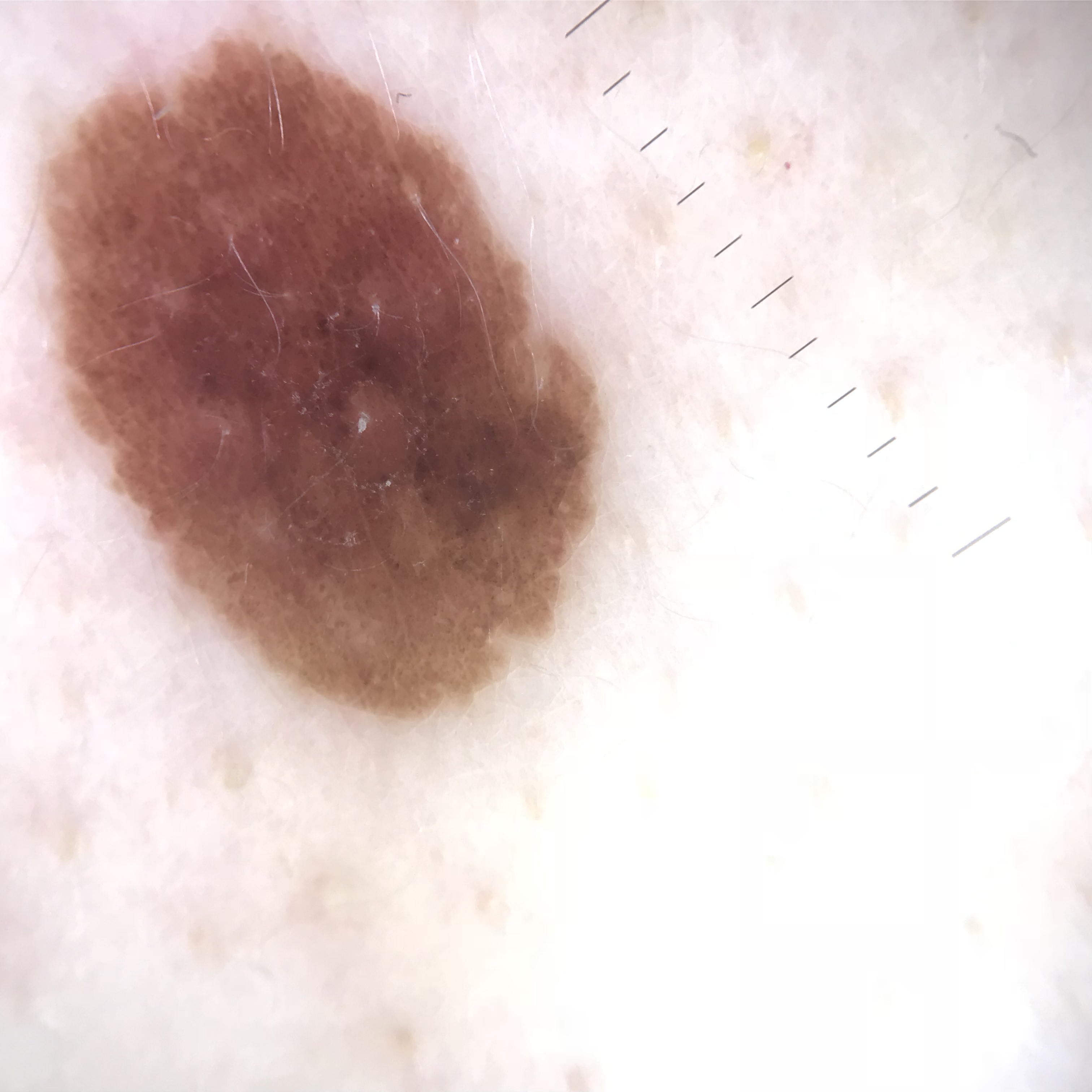Consistent with a dysplastic junctional nevus.